Dermoscopy of a skin lesion: 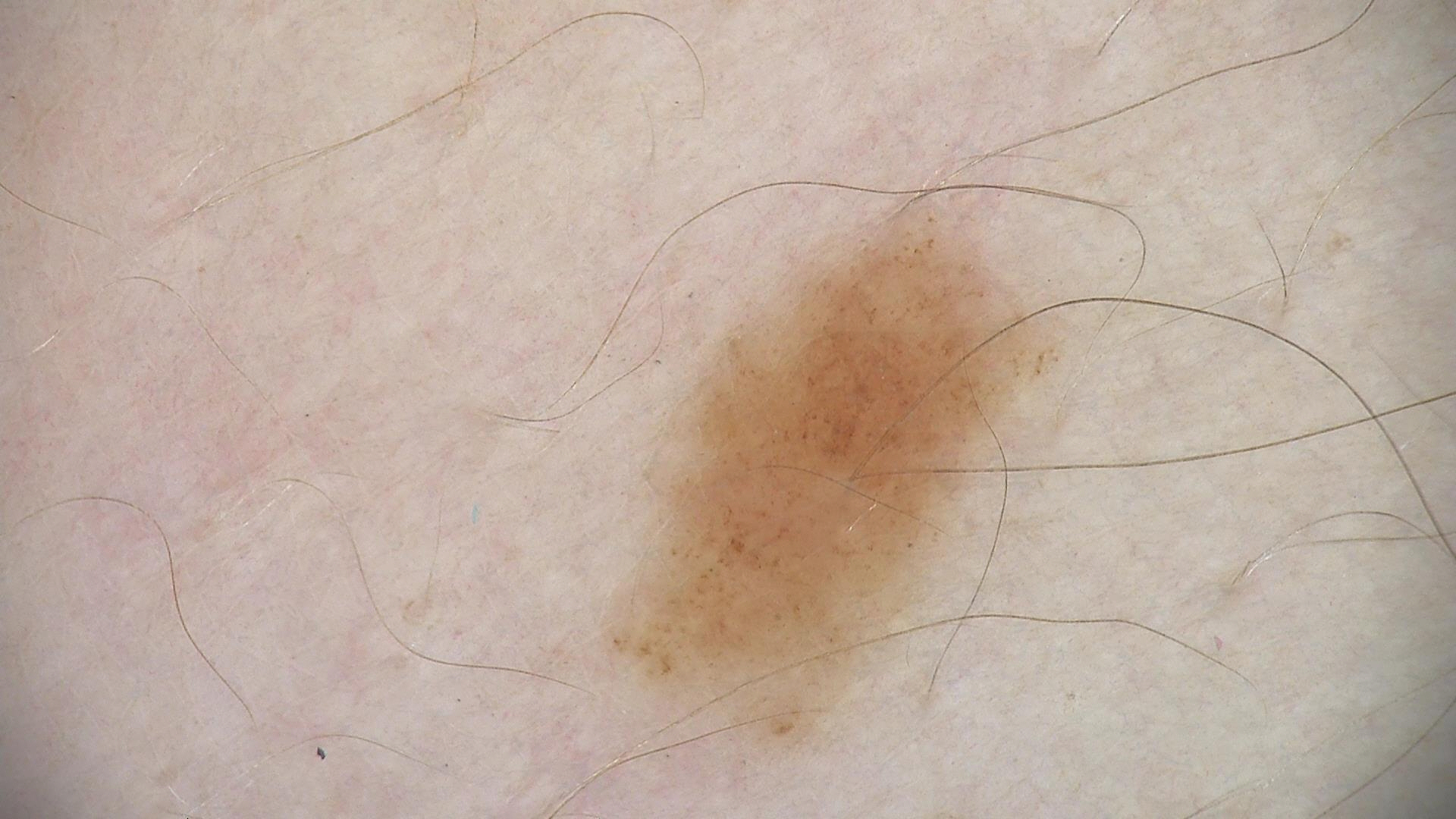Impression:
Labeled as a dysplastic junctional nevus.